A dermoscopy image of a single skin lesion · the patient is a male approximately 75 years of age:
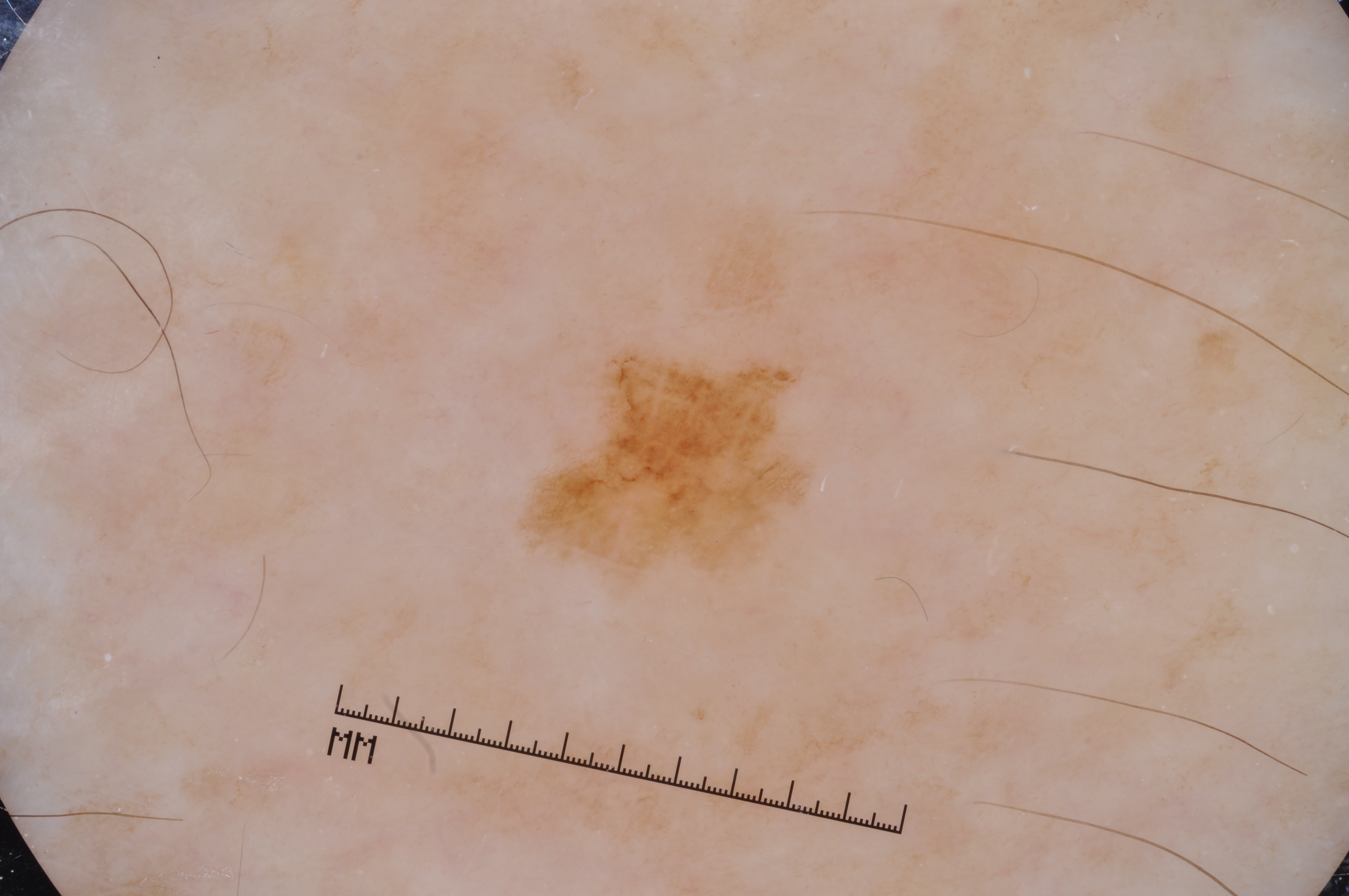  dermoscopic_features:
    present:
      - pigment network
    absent:
      - negative network
      - milia-like cysts
      - streaks
  lesion_location:
    bbox_xyxy:
      - 518
      - 341
      - 813
      - 587
  diagnosis:
    name: melanoma
    malignancy: malignant
    lineage: melanocytic
    provenance: histopathology